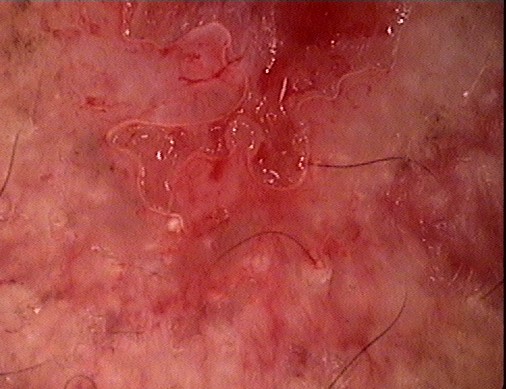* modality · dermoscopy
* pathology · basal cell carcinoma (biopsy-proven)